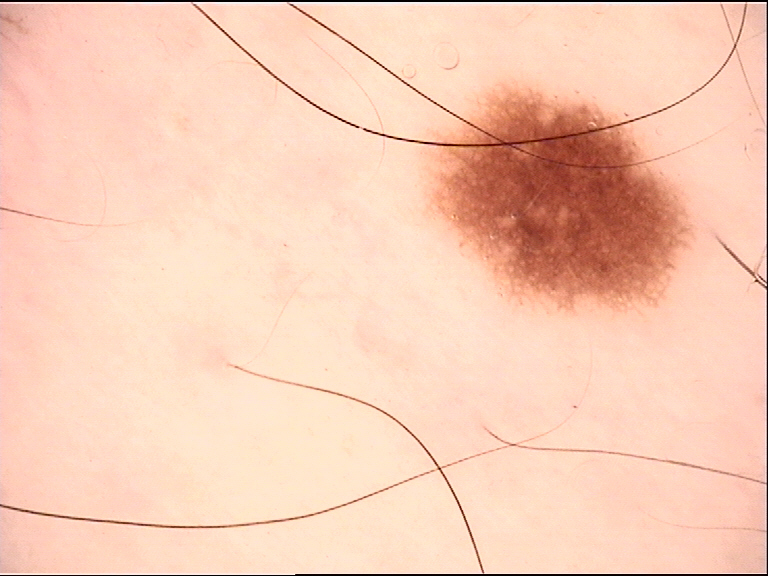image — dermoscopy | diagnosis — dysplastic junctional nevus (expert consensus).